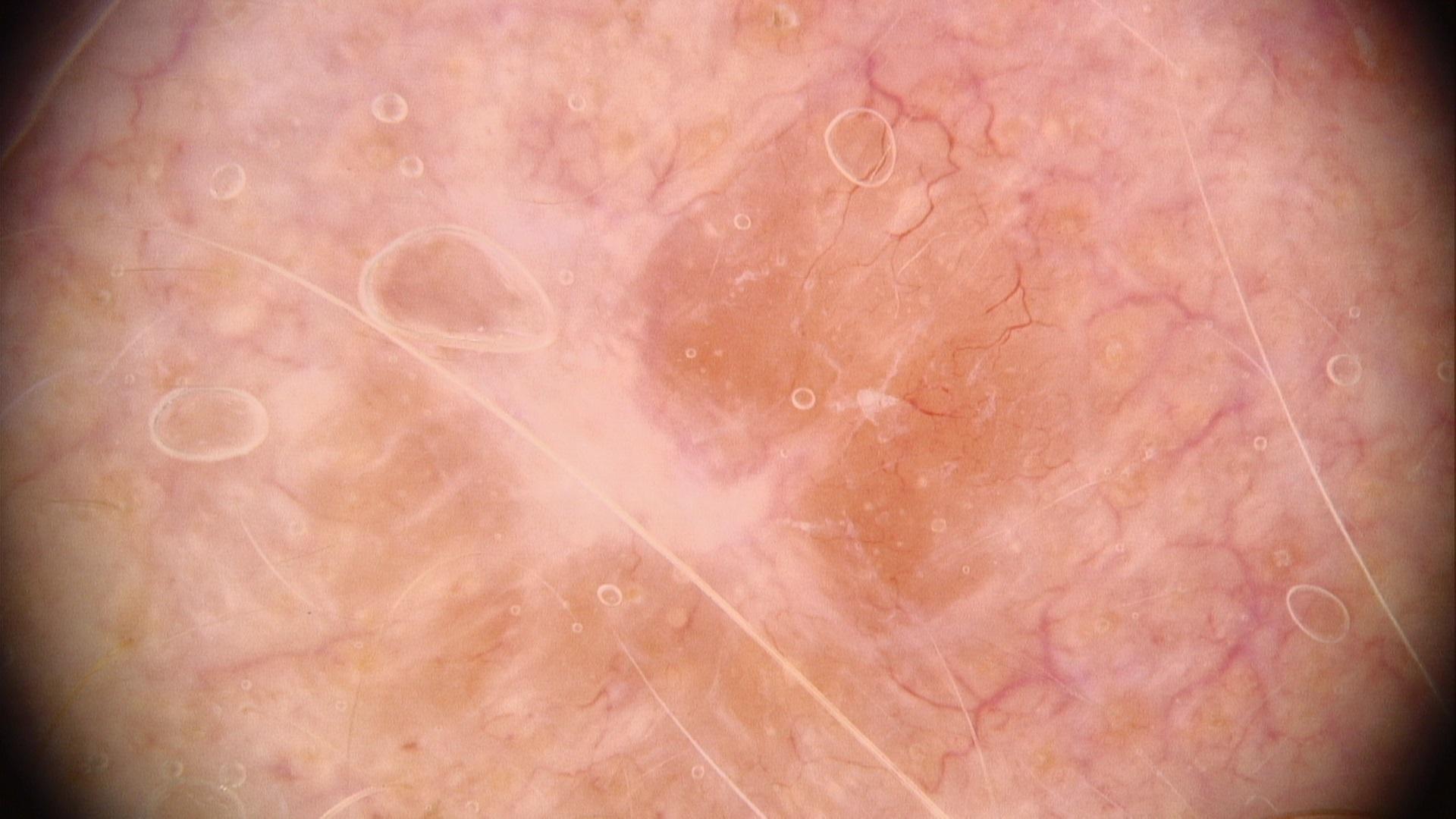The patient was assessed as Fitzpatrick I. Contact-polarized dermoscopy of a skin lesion. A female patient roughly 55 years of age. The chart records a previous melanoma. Histopathological examination showed a basal cell carcinoma.